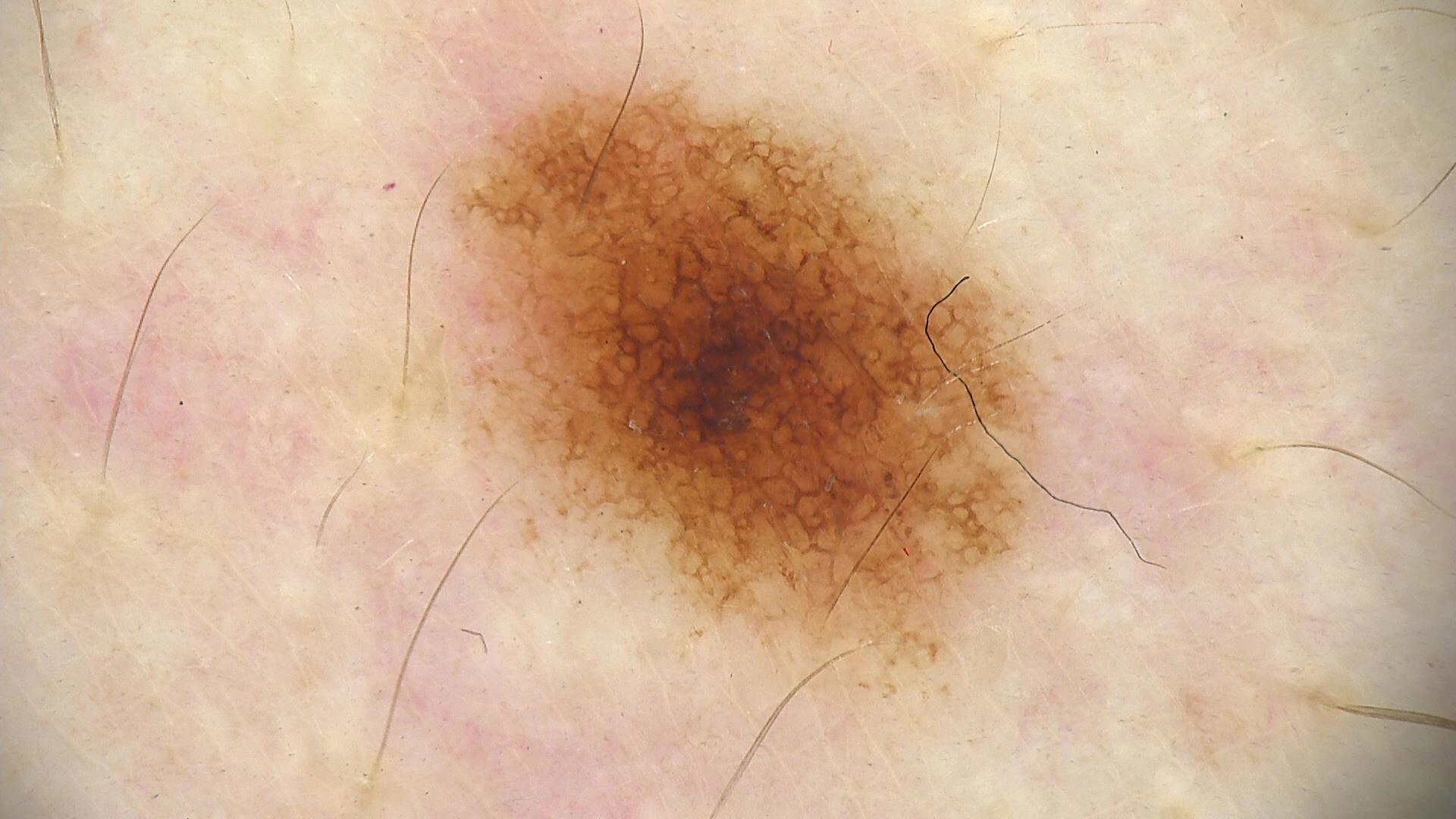modality — dermoscopy; class — dysplastic junctional nevus (expert consensus).